A dermatoscopic image of a skin lesion: 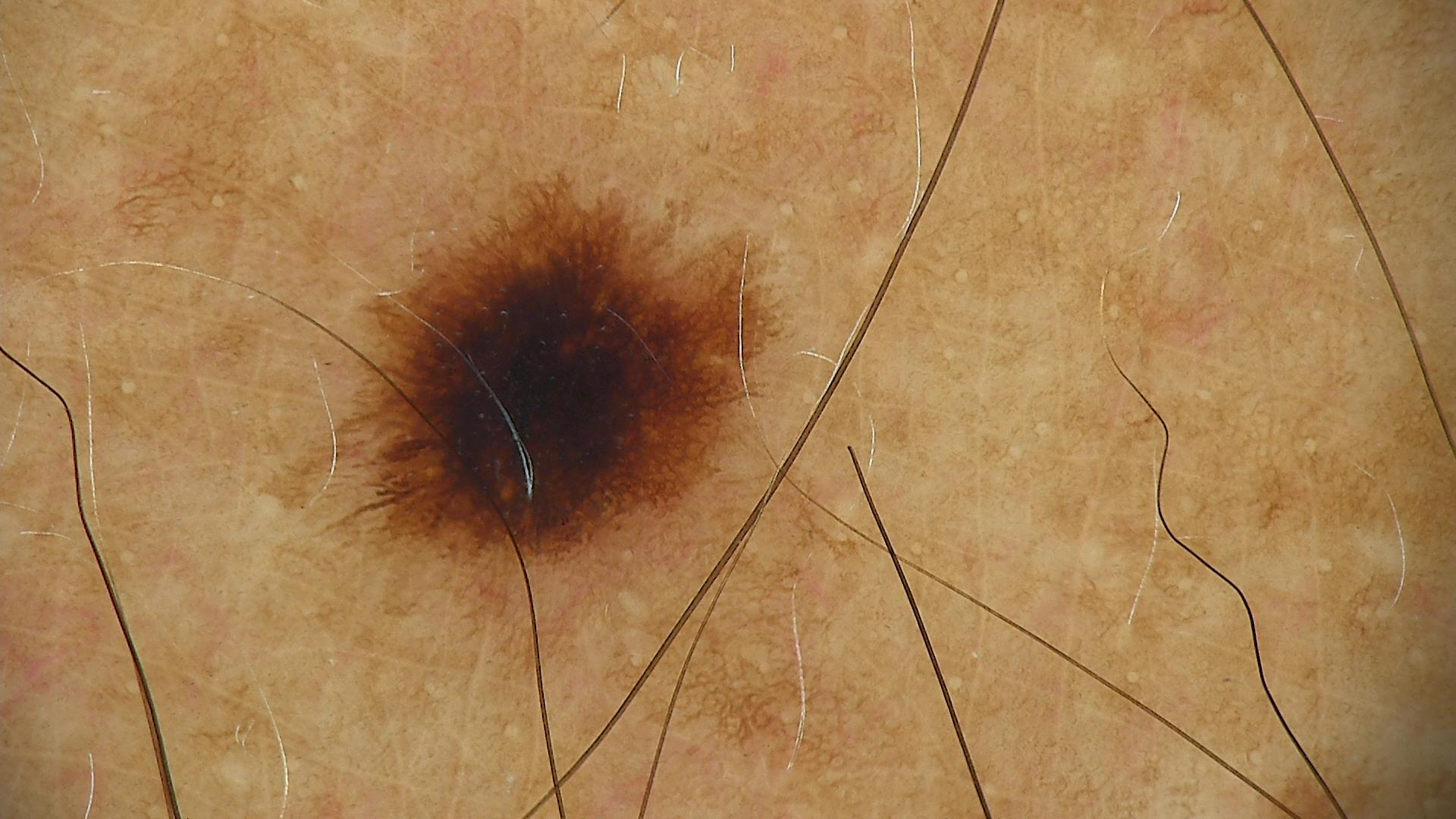Labeled as a benign lesion — a dysplastic junctional nevus.